This is a close-up image: 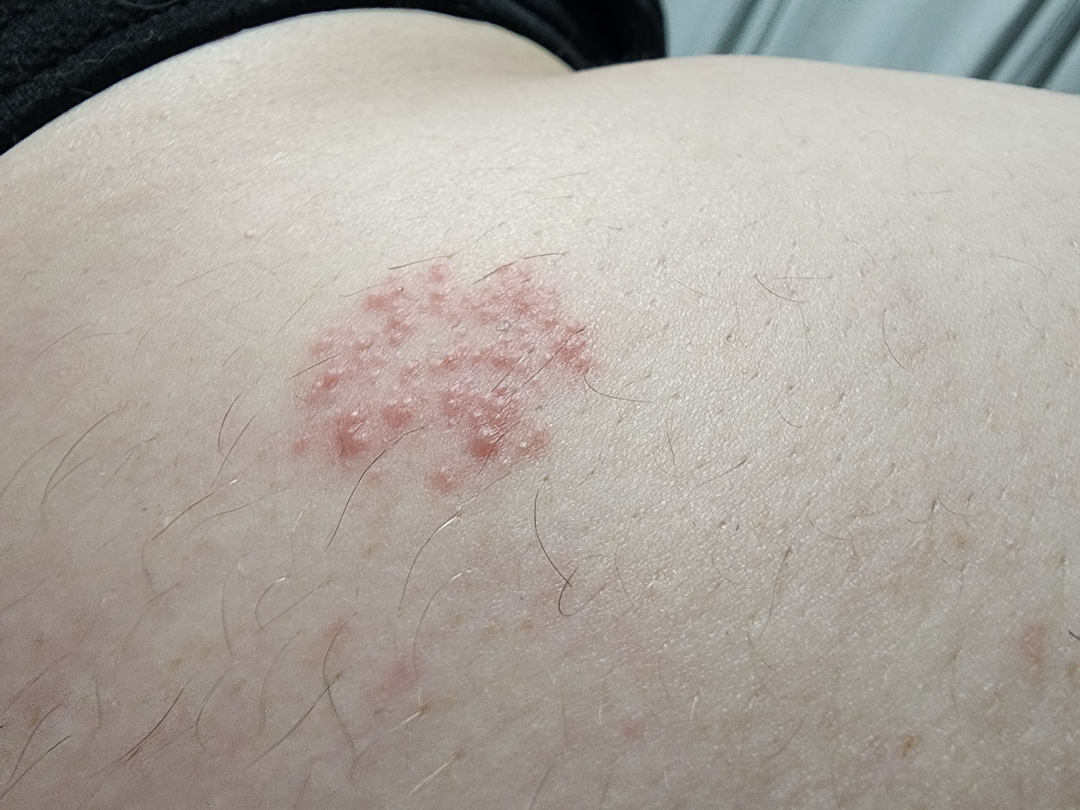Q: What is the differential diagnosis?
A: the favored diagnosis is Herpes Simplex; with consideration of Herpes Zoster; less probable is Allergic Contact Dermatitis